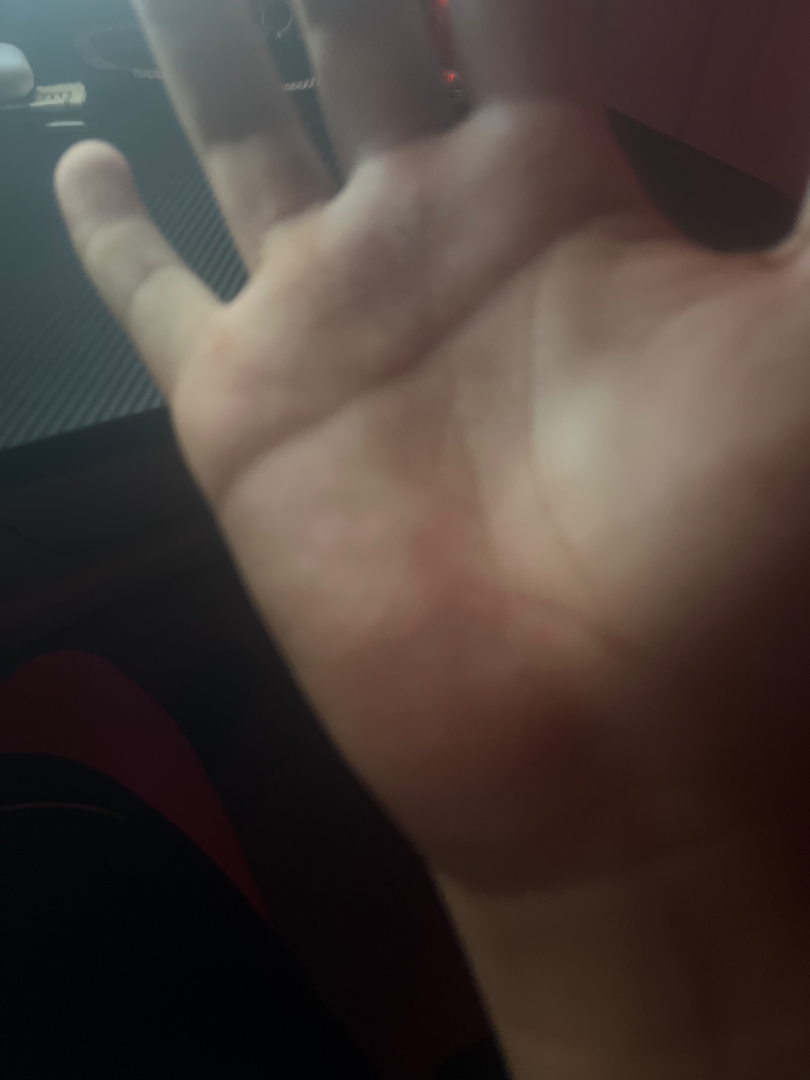The skin findings could not be characterized from the image.
A close-up photograph.
The patient indicates the condition has been present for about one day.
No associated systemic symptoms reported.
The patient indicates itching, burning and pain.
The patient indicates the lesion is rough or flaky and raised or bumpy.
Located on the palm.